Dermoscopy of a skin lesion.
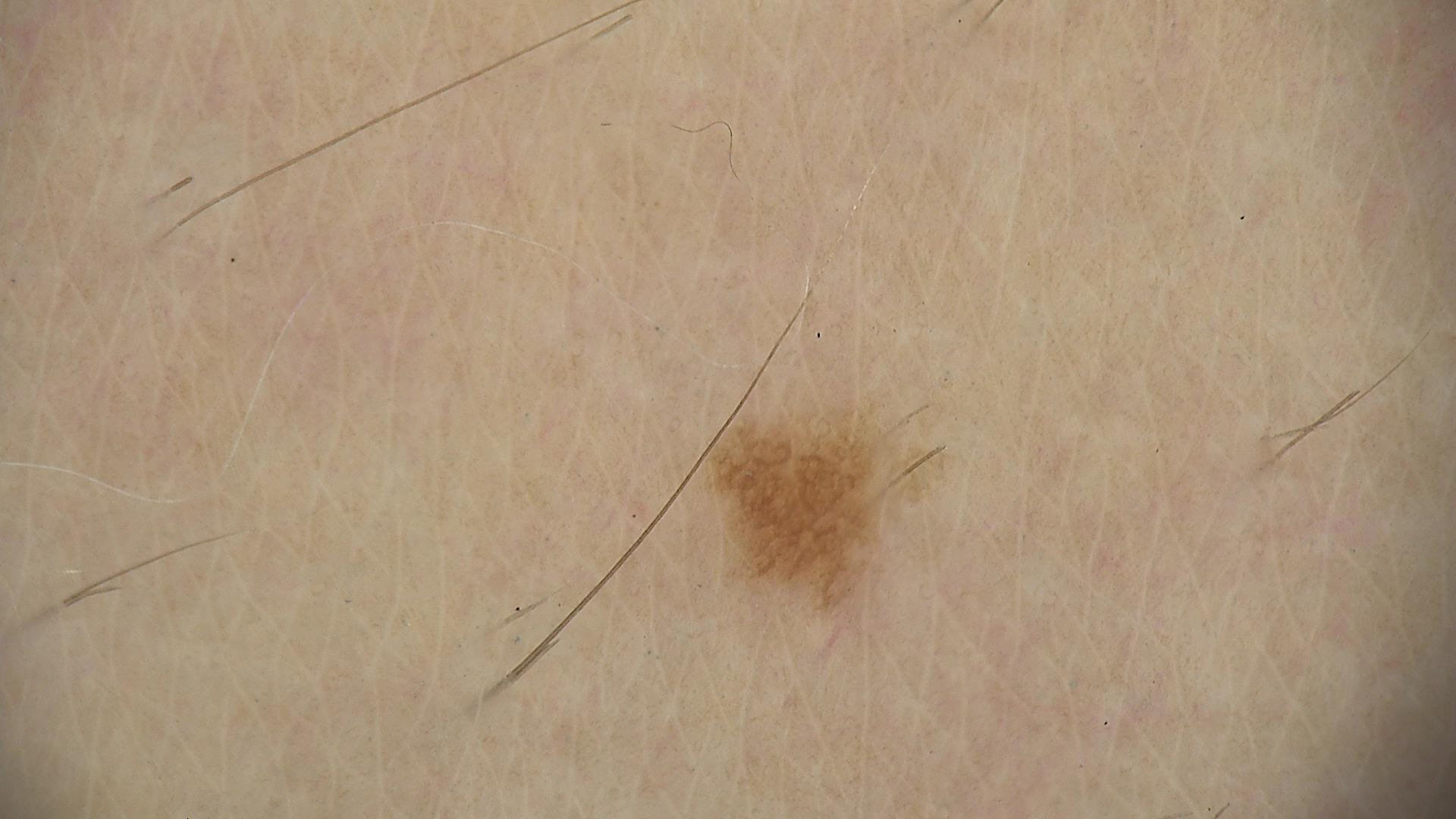diagnosis — junctional nevus (expert consensus).